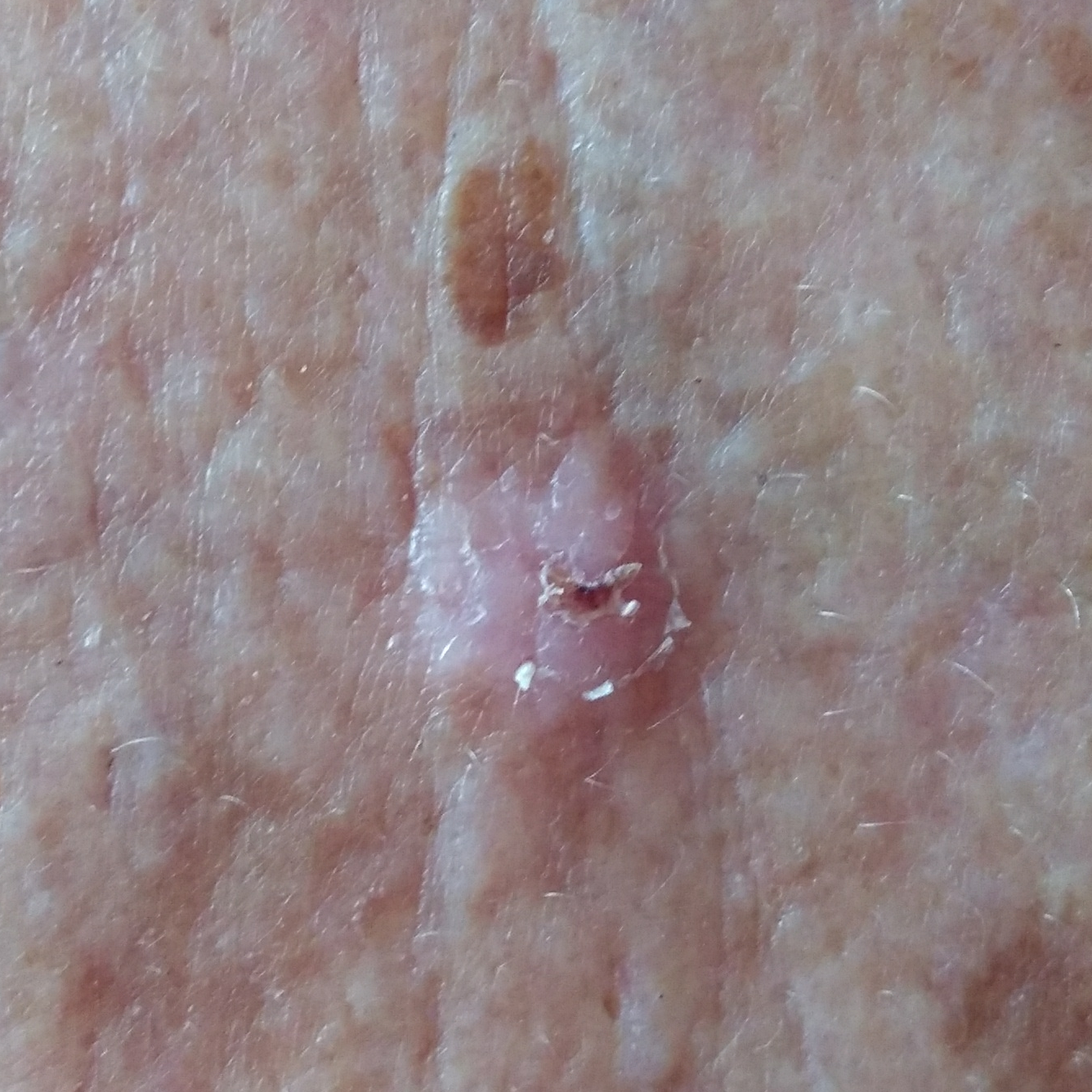A clinical photo of a skin lesion taken with a smartphone. The patient reports that the lesion itches, is elevated, and has bled. Biopsy-confirmed as a squamous cell carcinoma.